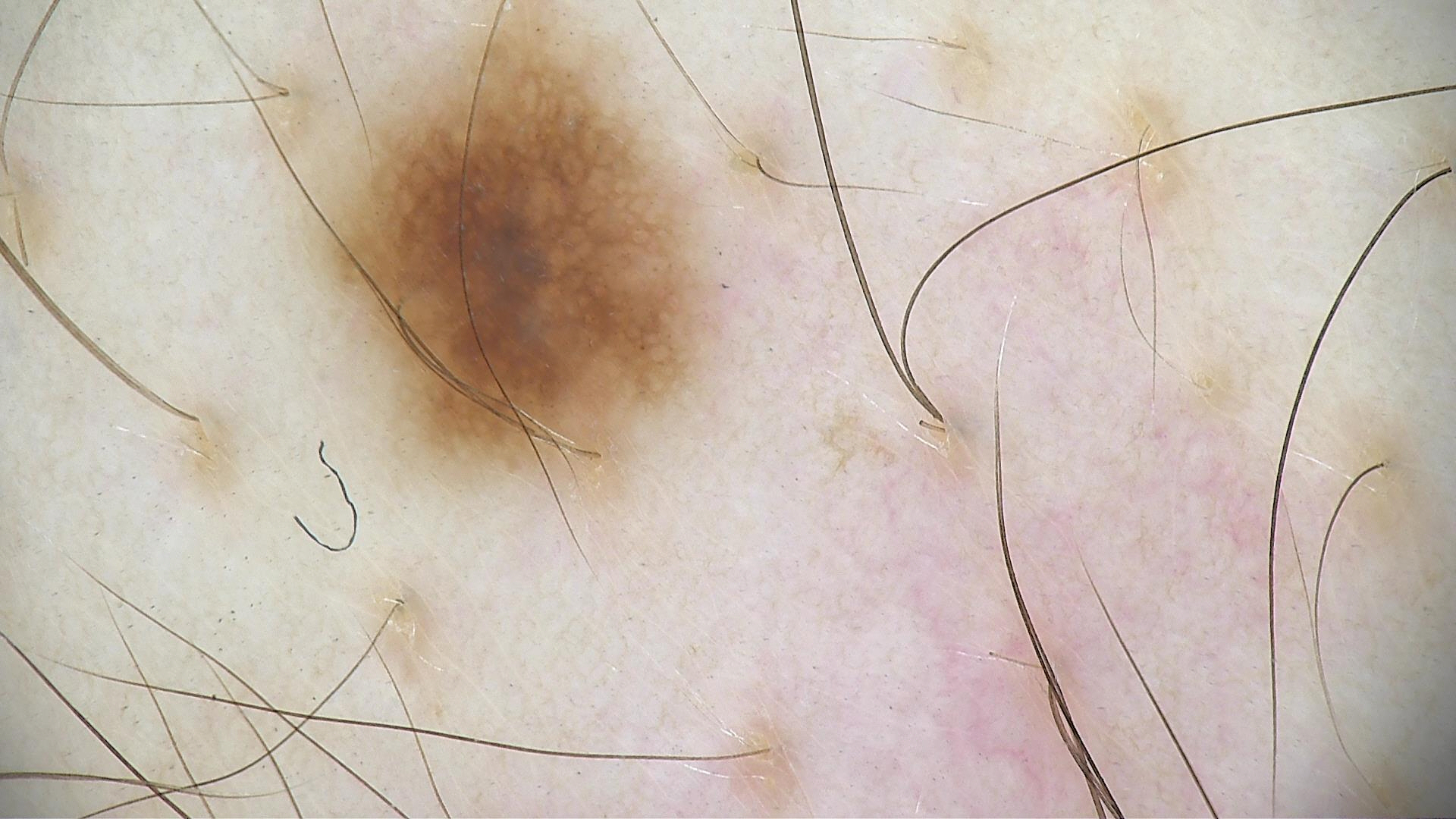Consistent with a dysplastic junctional nevus.